An image taken at a distance:
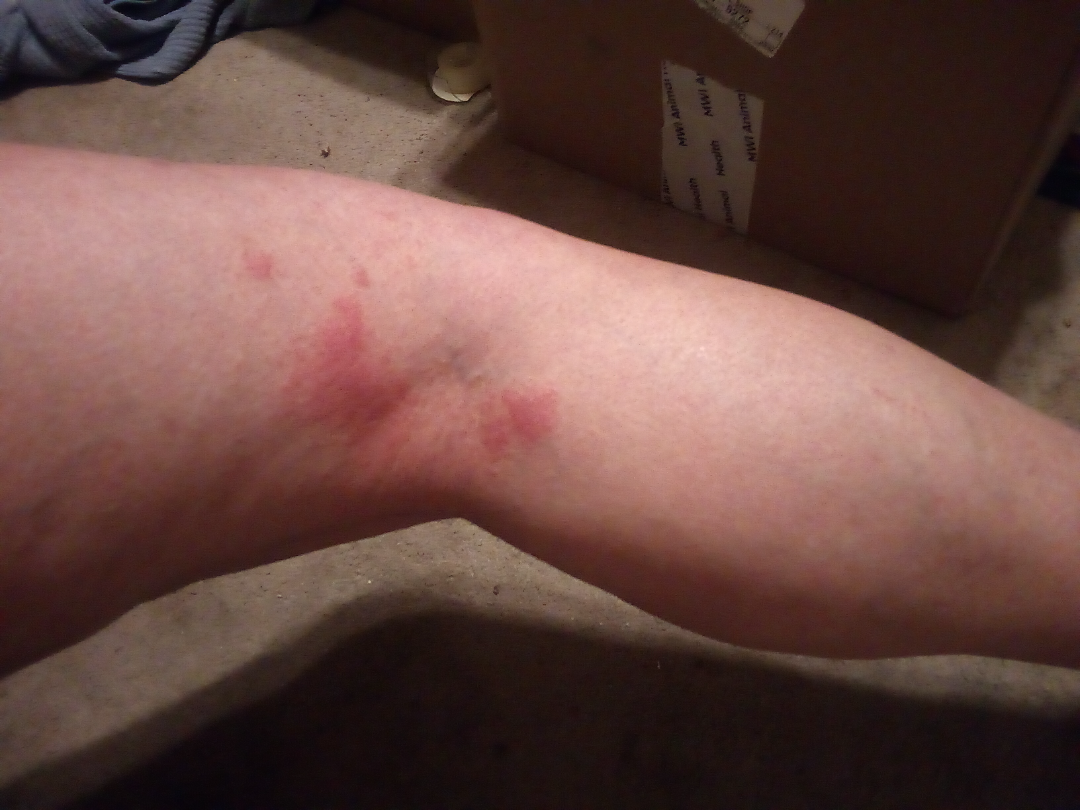Eczema (most likely); Allergic Contact Dermatitis (considered).